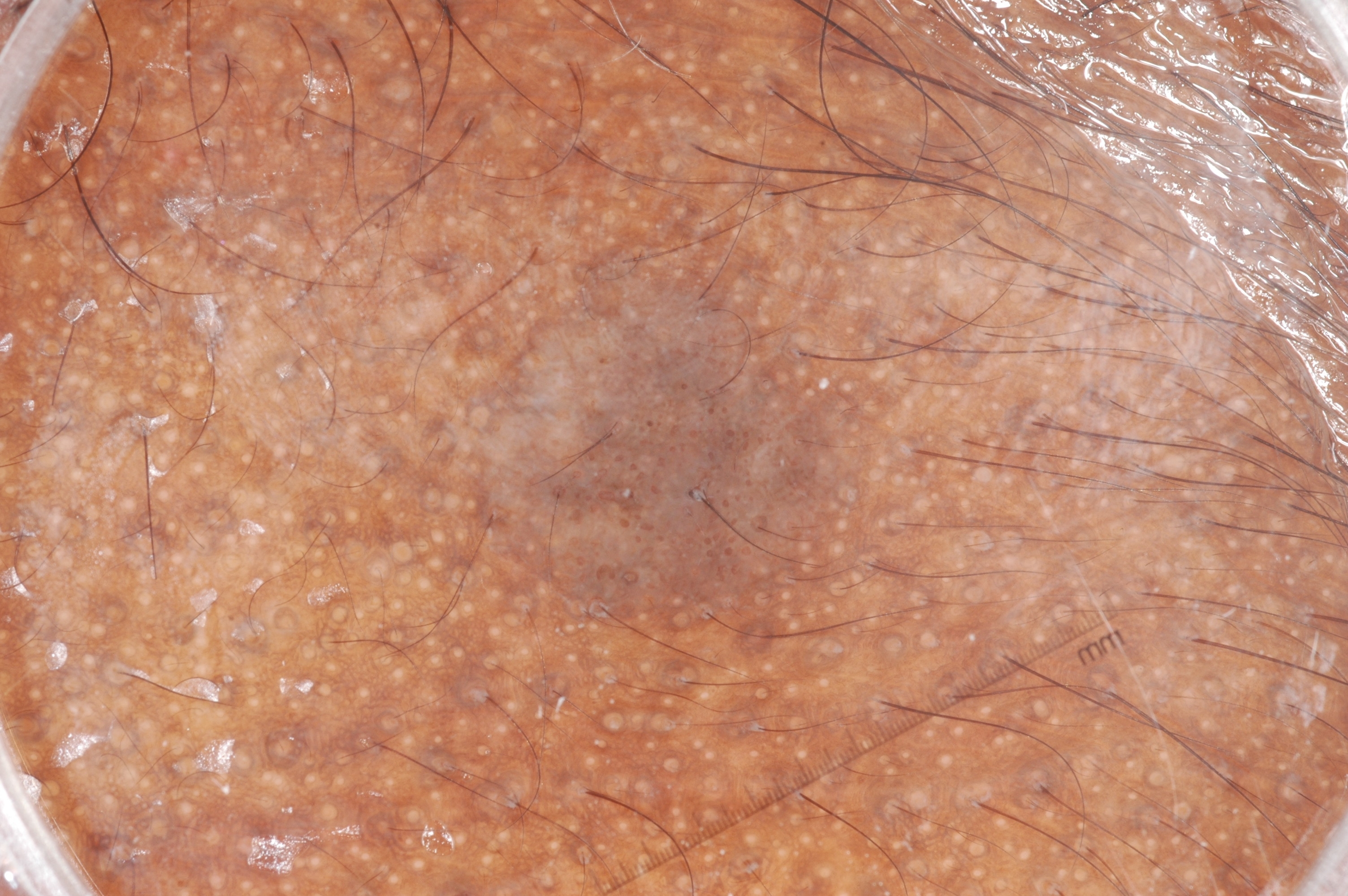| feature | finding |
|---|---|
| imaging | dermoscopic image |
| lesion location | 413 233 903 674 |
| lesion size | moderate |
| absent dermoscopic features | milia-like cysts, negative network, streaks, and pigment network |
| impression | a seborrheic keratosis, a benign lesion |